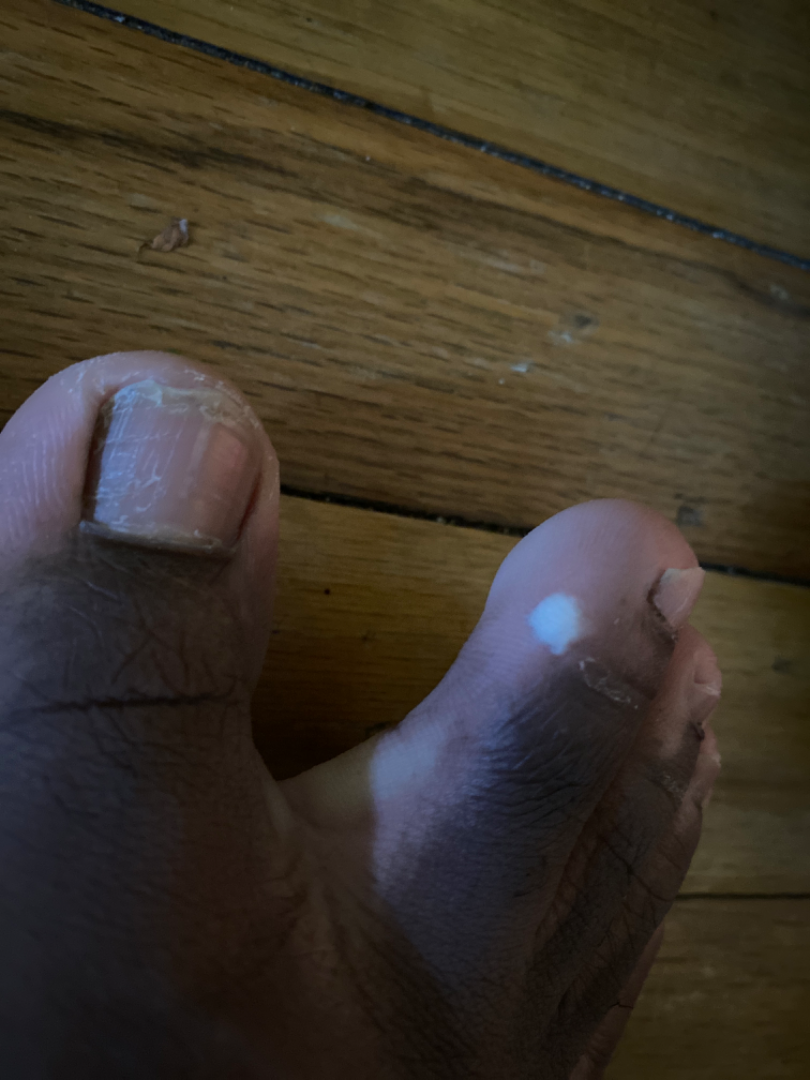The lesion is described as fluid-filled. The lesion is associated with bothersome appearance. This image was taken at an angle. Present for about one day. The patient is 18–29, male. The lesion involves the top or side of the foot.